A male subject aged approximately 35; a skin lesion imaged with a dermatoscope:
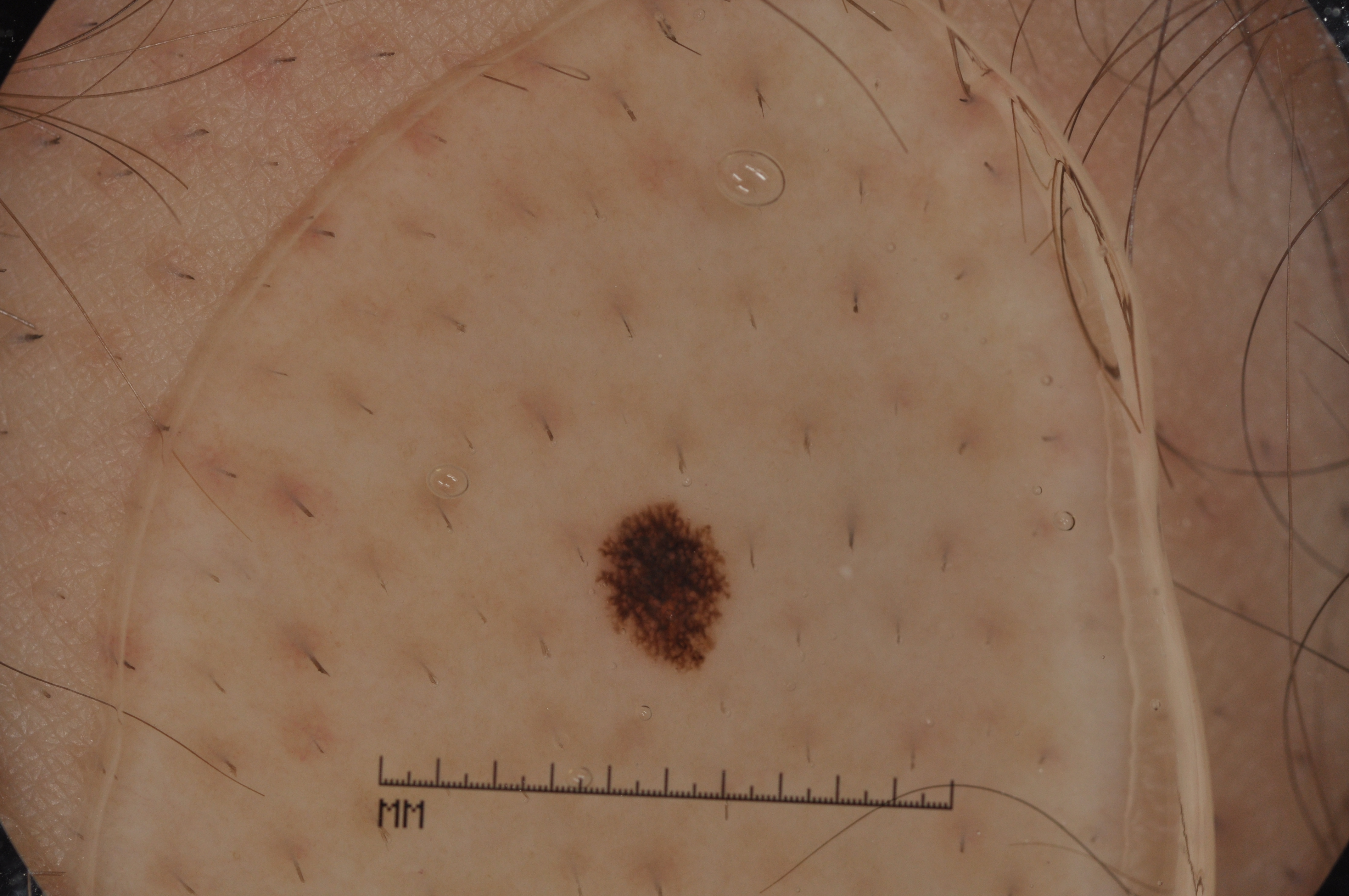In (x1, y1, x2, y2) order, the lesion's extent is [601,511,727,658]. The dermoscopic pattern shows pigment network. Consistent with a melanocytic nevus, a benign lesion.